A female subject 75 years of age · acquired for a research image collection, with no referral diagnosis · a clinical photograph of a skin lesion: 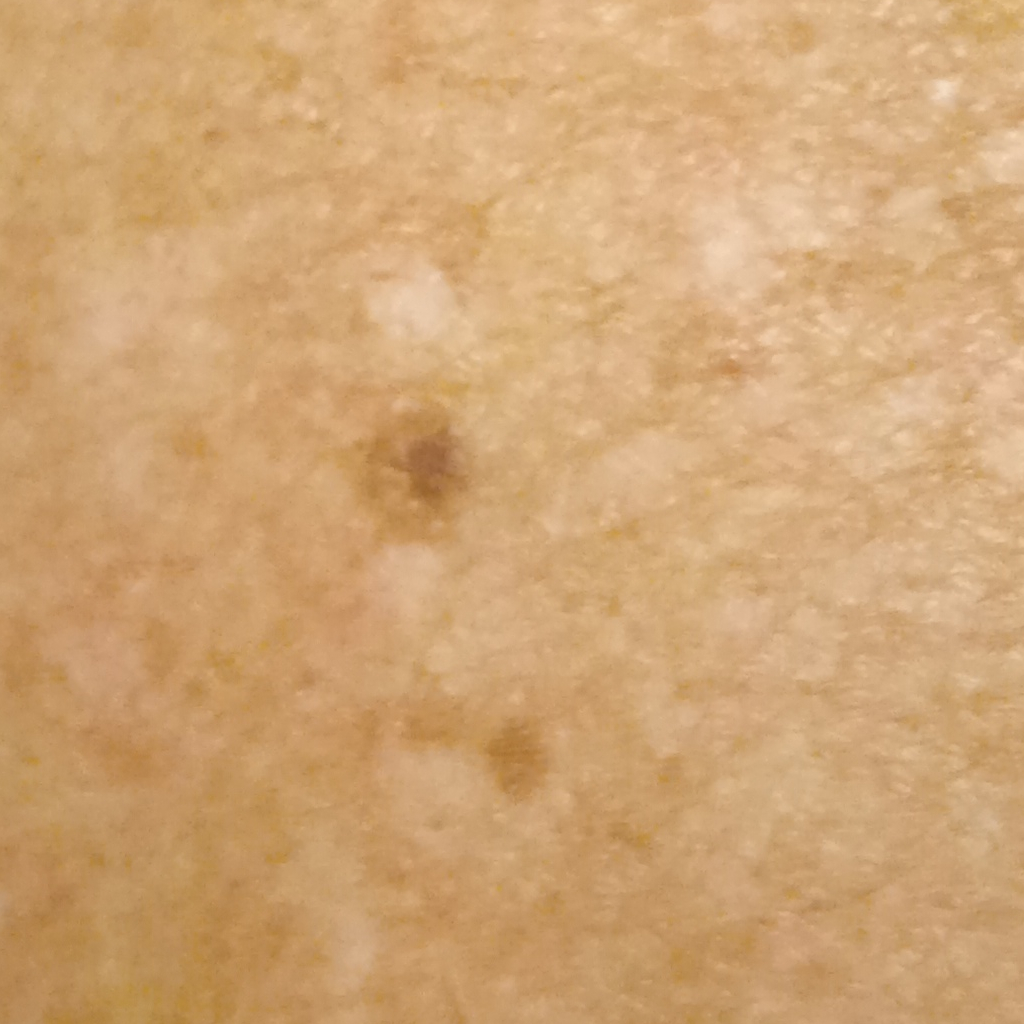site = the back | diameter = 2.7 mm | diagnosis = melanocytic nevus (dermatologist consensus).